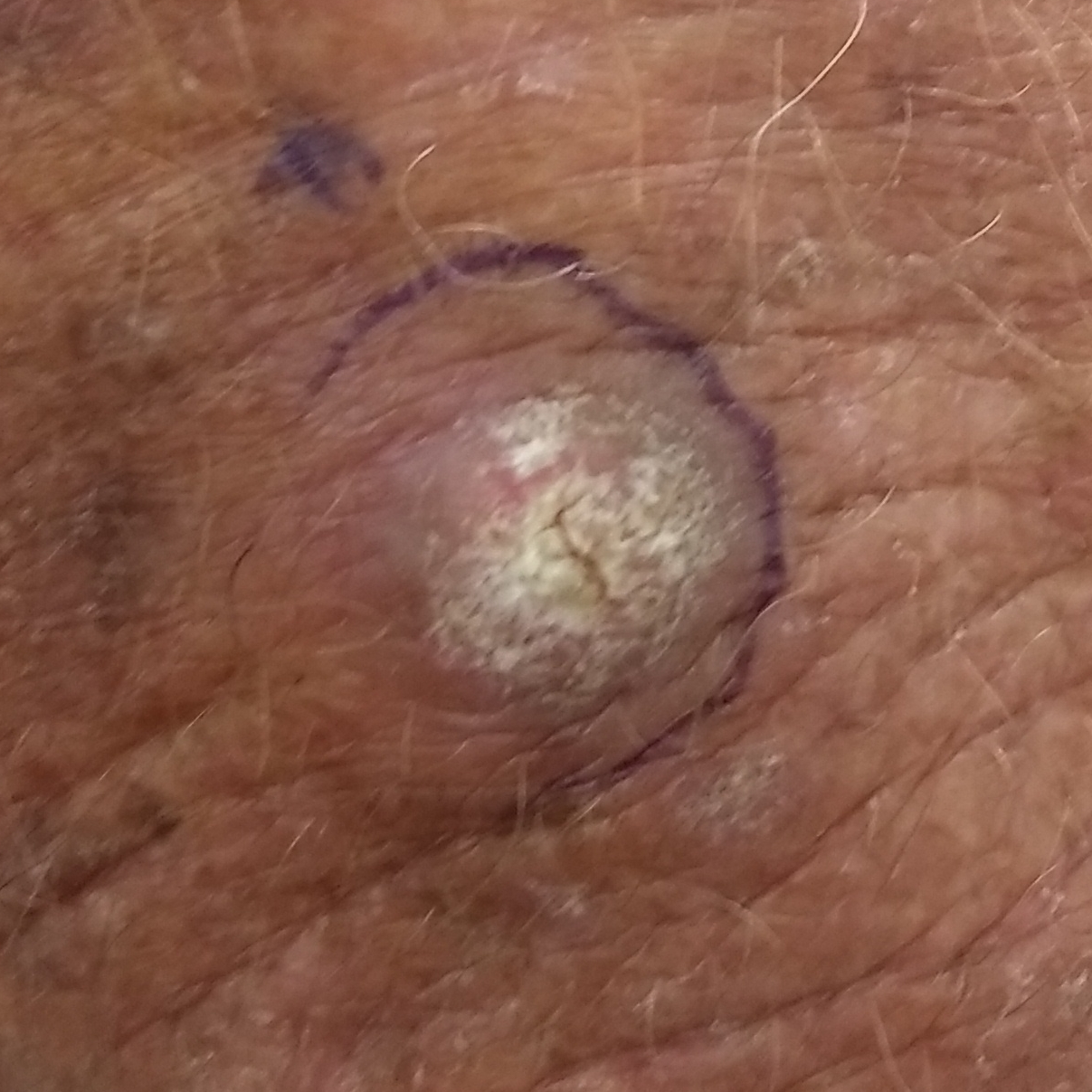A smartphone photograph of a skin lesion. The lesion measures 15 × 10 mm. Biopsy-confirmed as a squamous cell carcinoma.